The contributor notes the lesion is rough or flaky and raised or bumpy · the lesion is associated with bothersome appearance · a close-up photograph · located on the head or neck · associated systemic symptoms include fatigue · skin tone: FST II; lay graders estimated a Monk skin tone scale of 2.
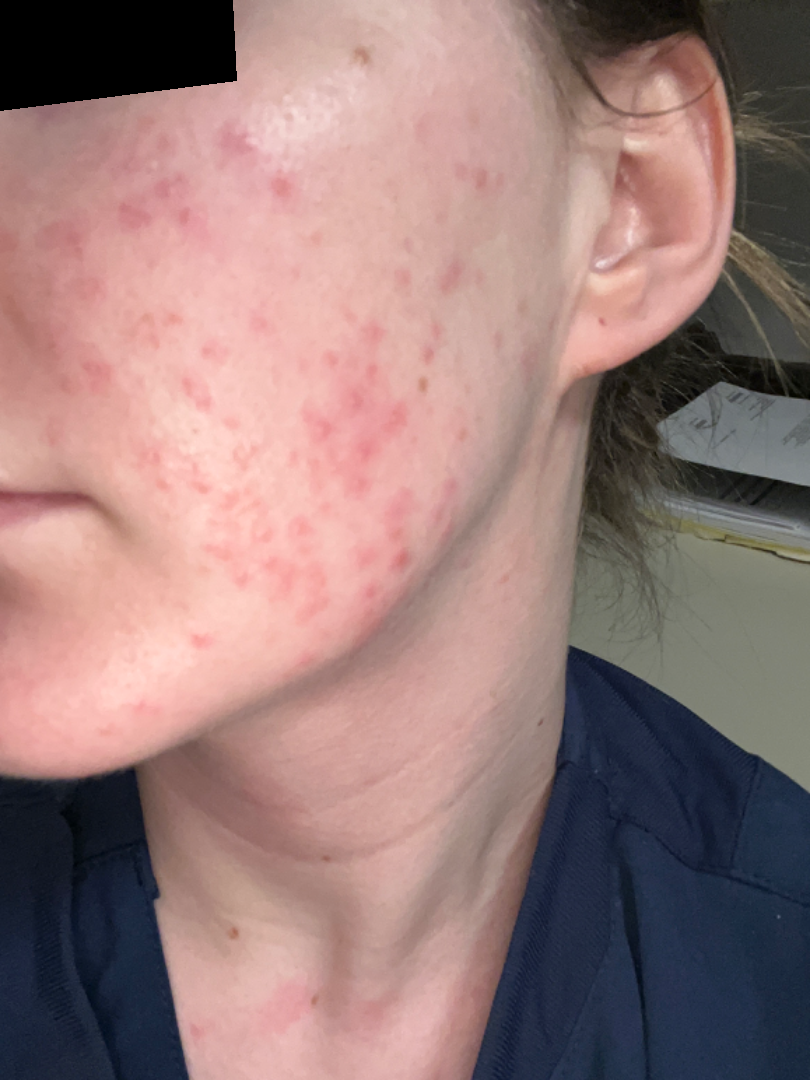Review:
One reviewing dermatologist: favoring Acne; possibly Rosacea.